FST I; human graders estimated a Monk Skin Tone of 2 · this is a close-up image:
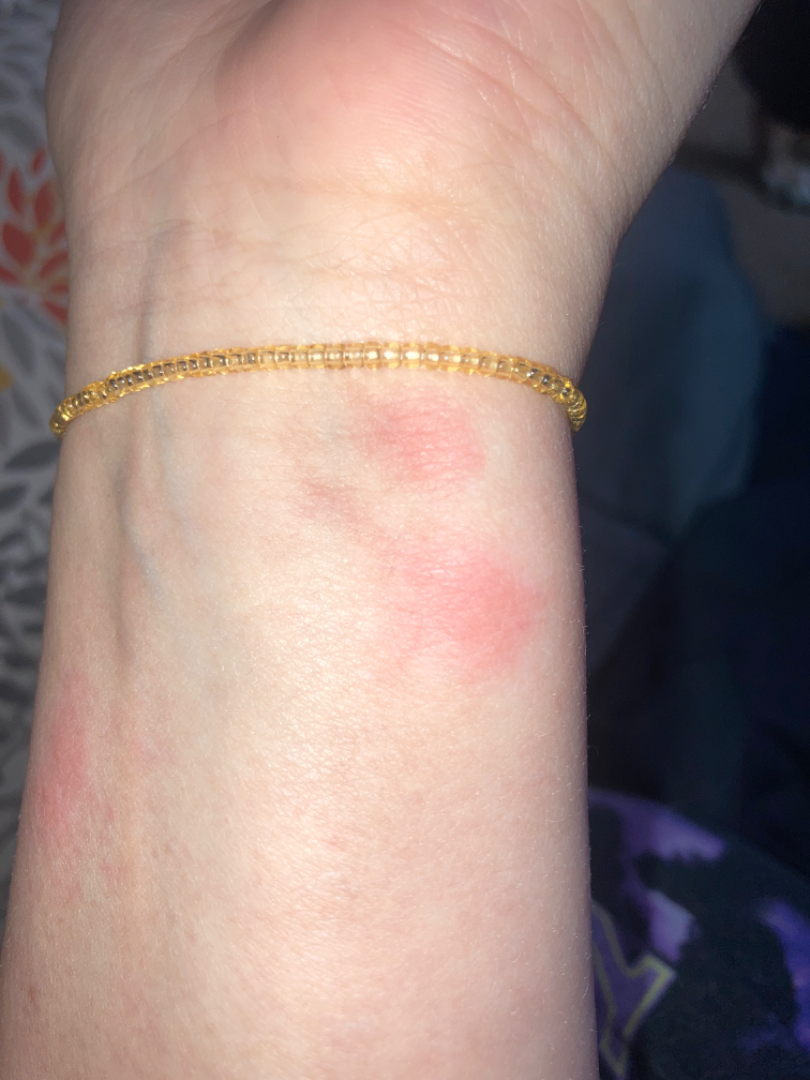On remote review of the image: Insect Bite (considered); Eczema (considered); Allergic Contact Dermatitis (considered).